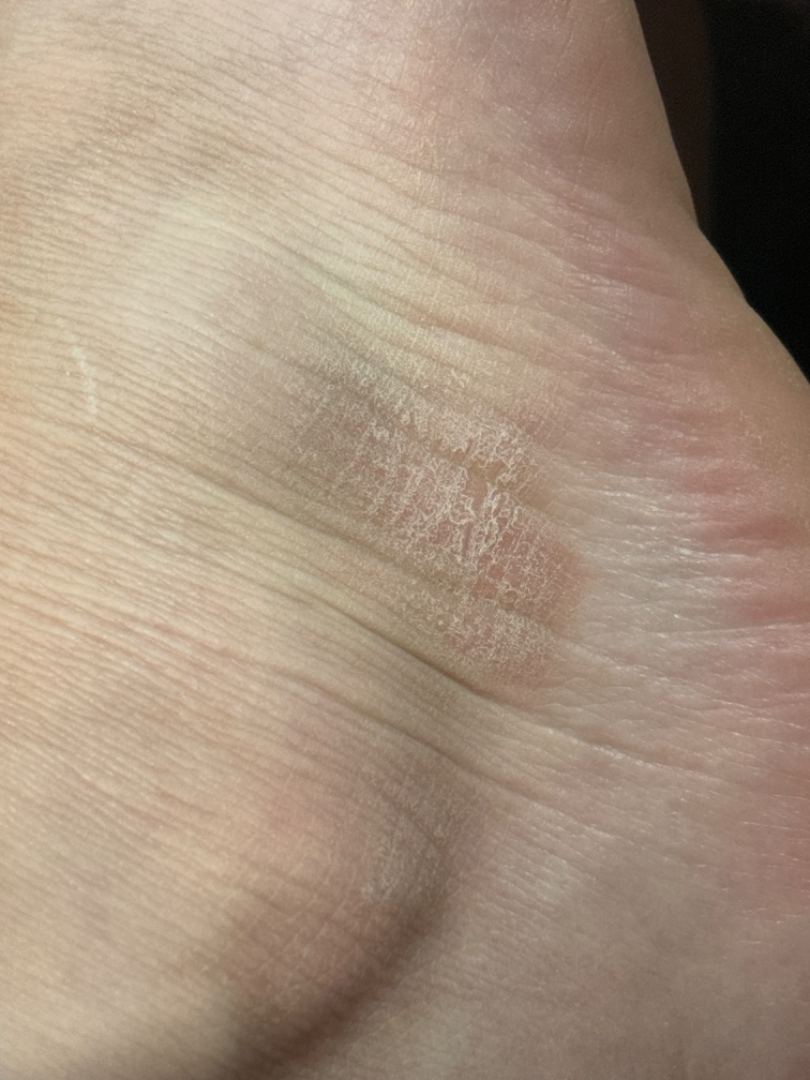Notes:
– view · close-up
– dermatologist impression · Lichen Simplex Chronicus (leading); Psoriasis (considered); Eczema (less likely)